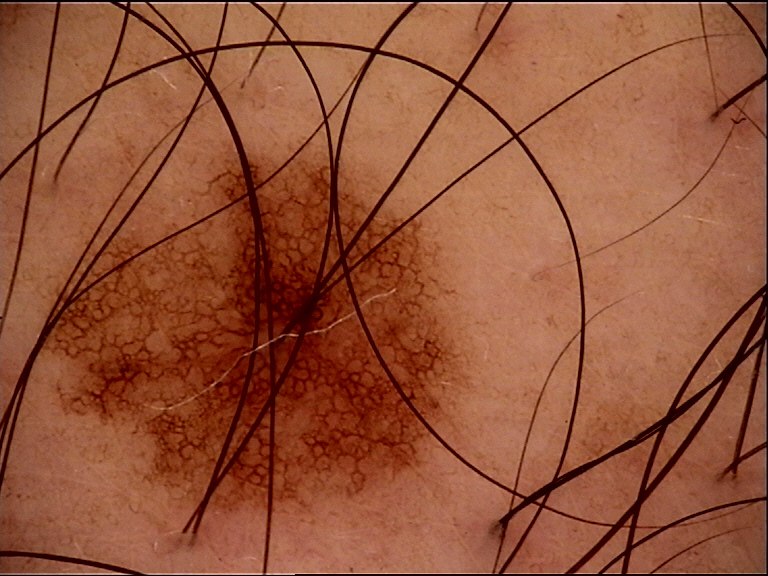label = junctional nevus (expert consensus).